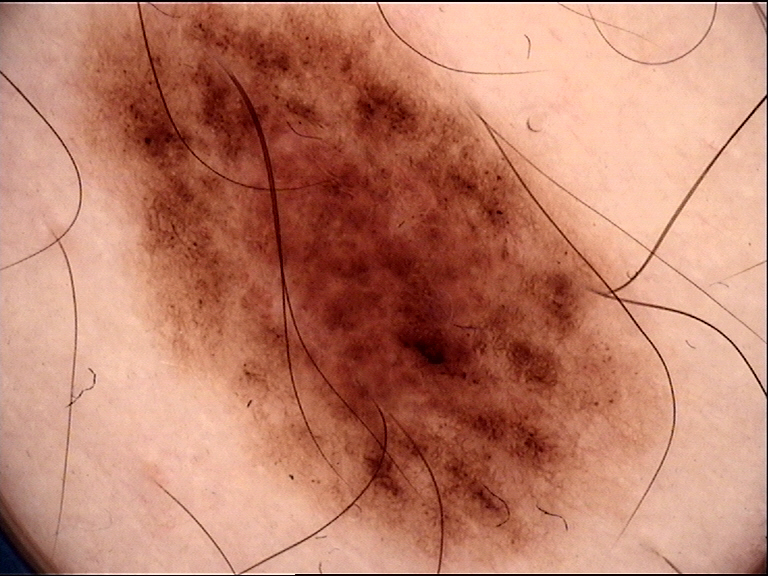Diagnosed as a dysplastic compound nevus.